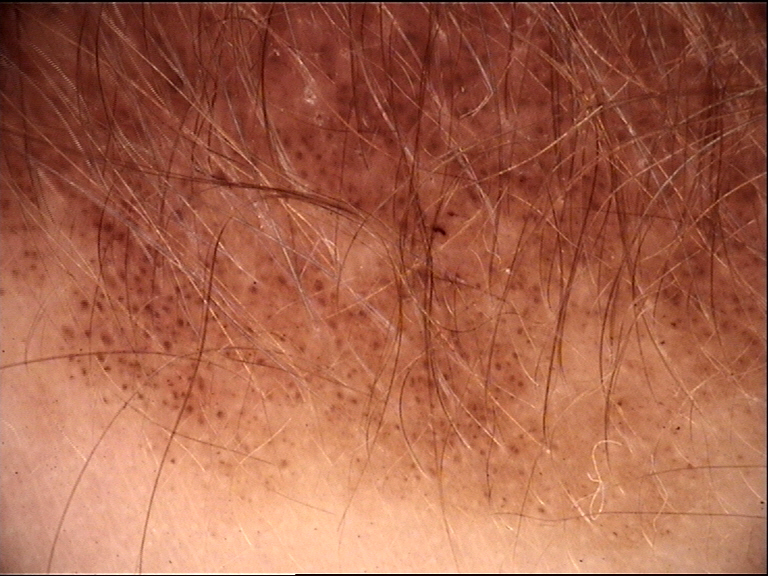Impression: Labeled as a banal lesion — a congenital junctional nevus.